The affected area is the head or neck; this image was taken at an angle; the subject is 18–29, female — 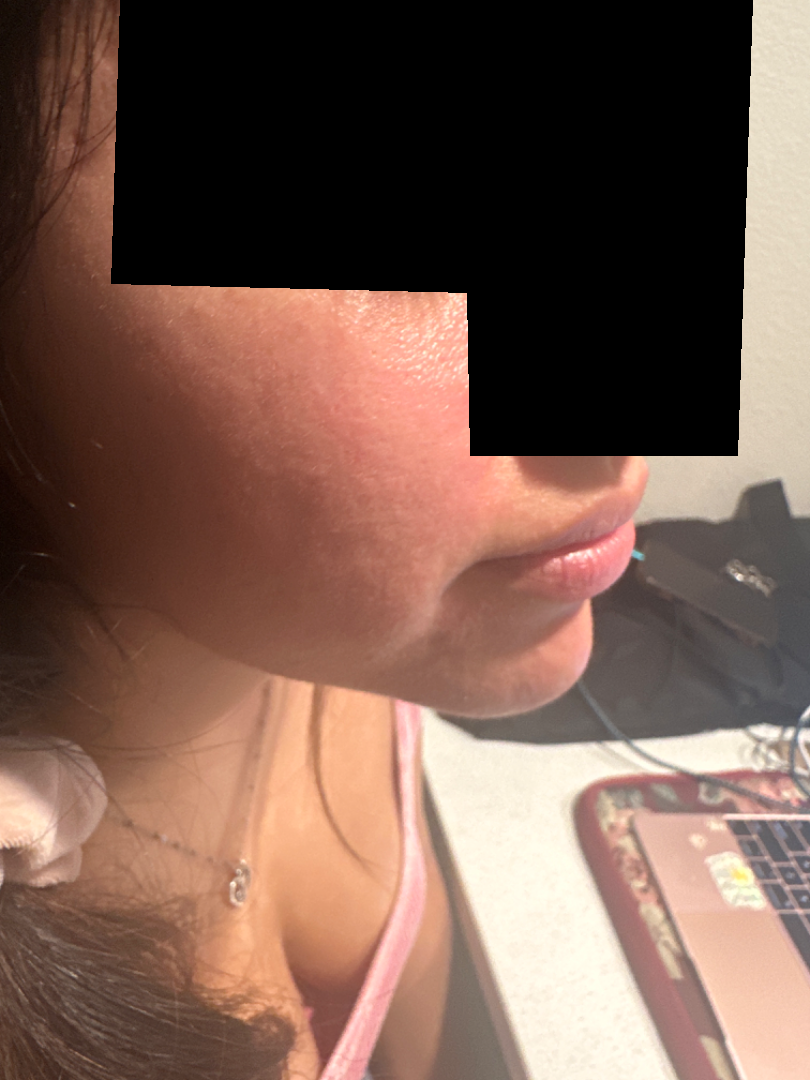Q: What is the differential diagnosis?
A: in keeping with Rosacea